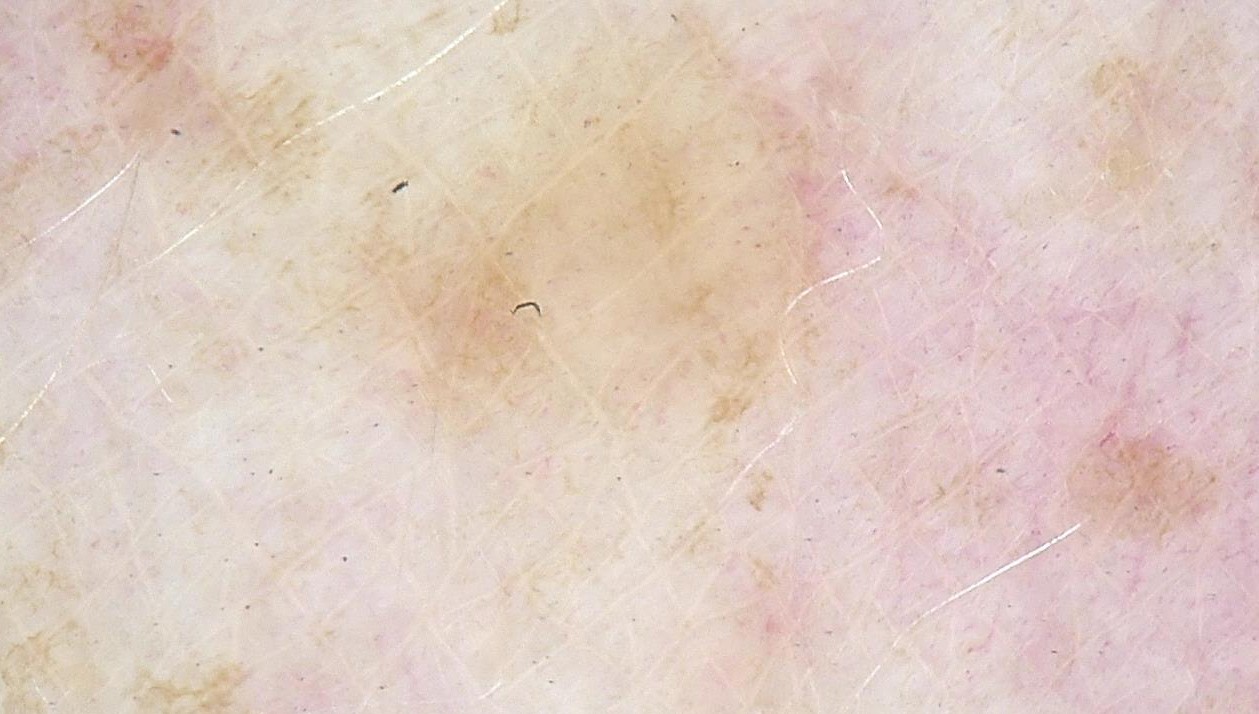{"diagnosis": {"name": "dermal nevus", "code": "db", "malignancy": "benign", "super_class": "melanocytic", "confirmation": "expert consensus"}}